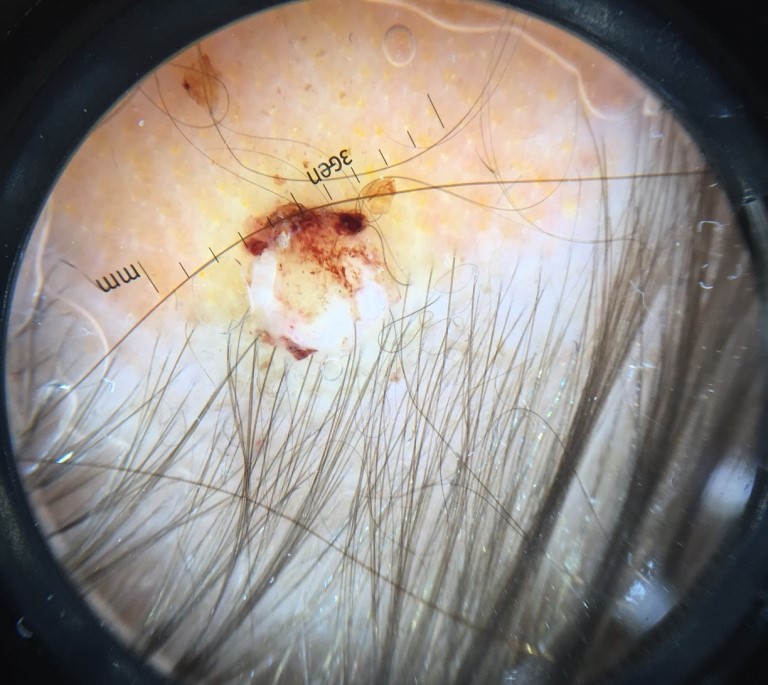Conclusion: Histopathology confirmed a malignancy — a squamous cell carcinoma.